A clinical close-up photograph of a skin lesion; a subject age 66 — 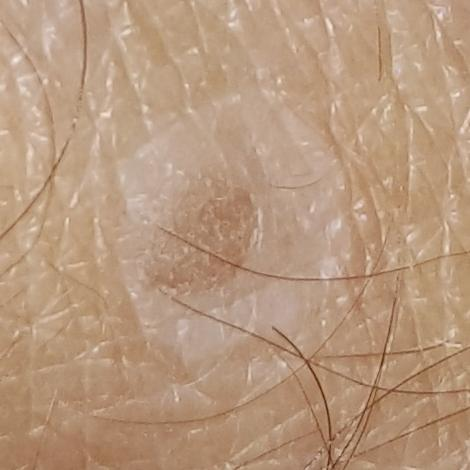Q: What is the anatomic site?
A: a forearm
Q: What does the patient describe?
A: growth
Q: What was the clinical impression?
A: nevus (clinical consensus)